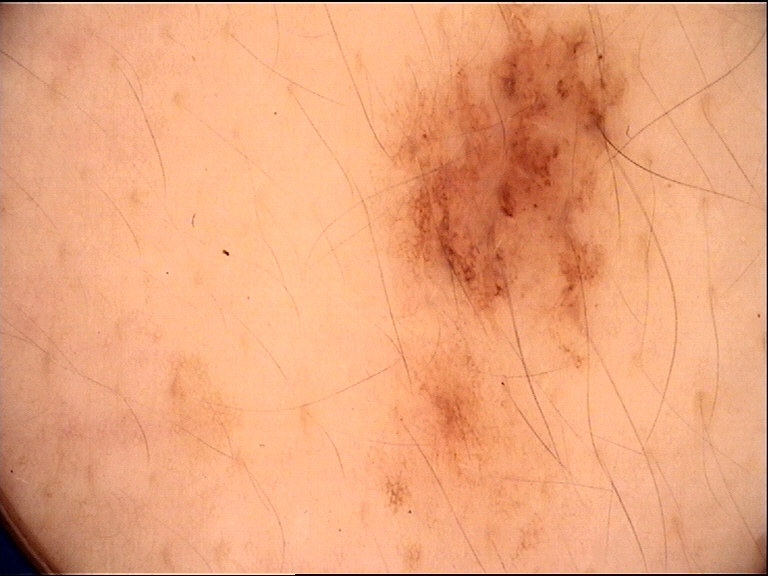Conclusion: Diagnosed as a dysplastic junctional nevus.